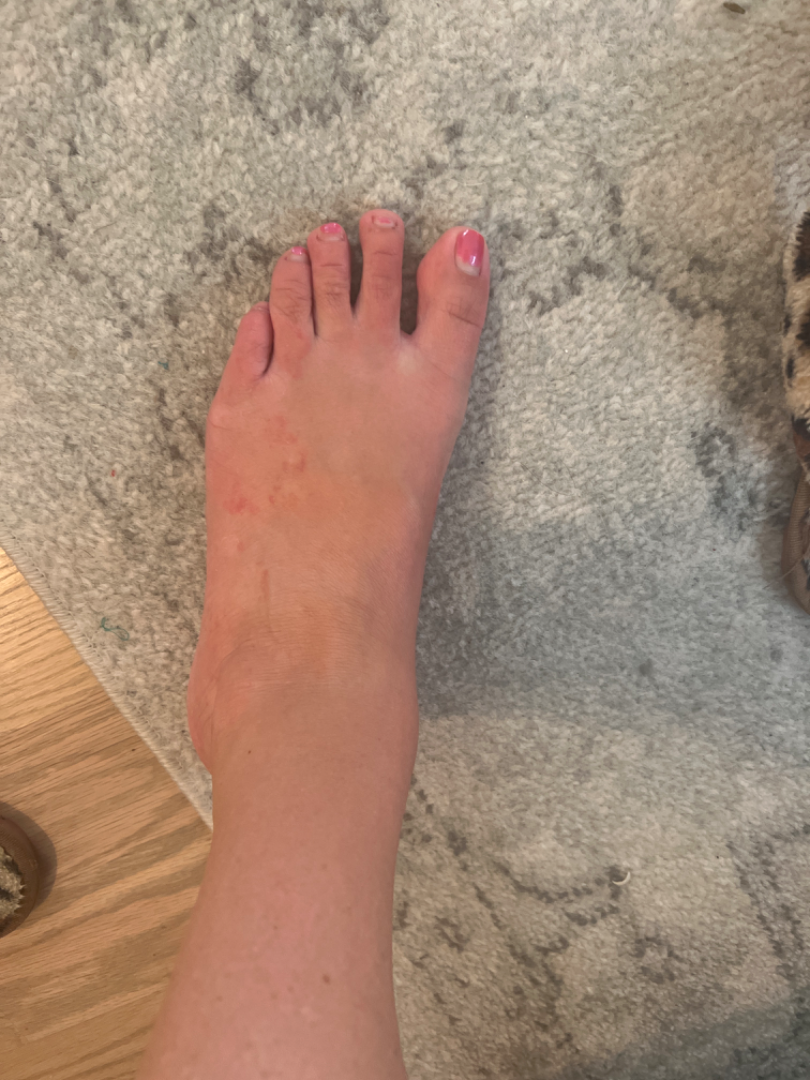The lesion involves the top or side of the foot.
The photo was captured at a distance.
Skin tone: non-clinician graders estimated 2 on the MST.
The patient notes the condition has been present for three to twelve months.
Single-reviewer assessment: Tinea and Cutaneous larva migrans were each considered, in no particular order; less probable is Eczema.